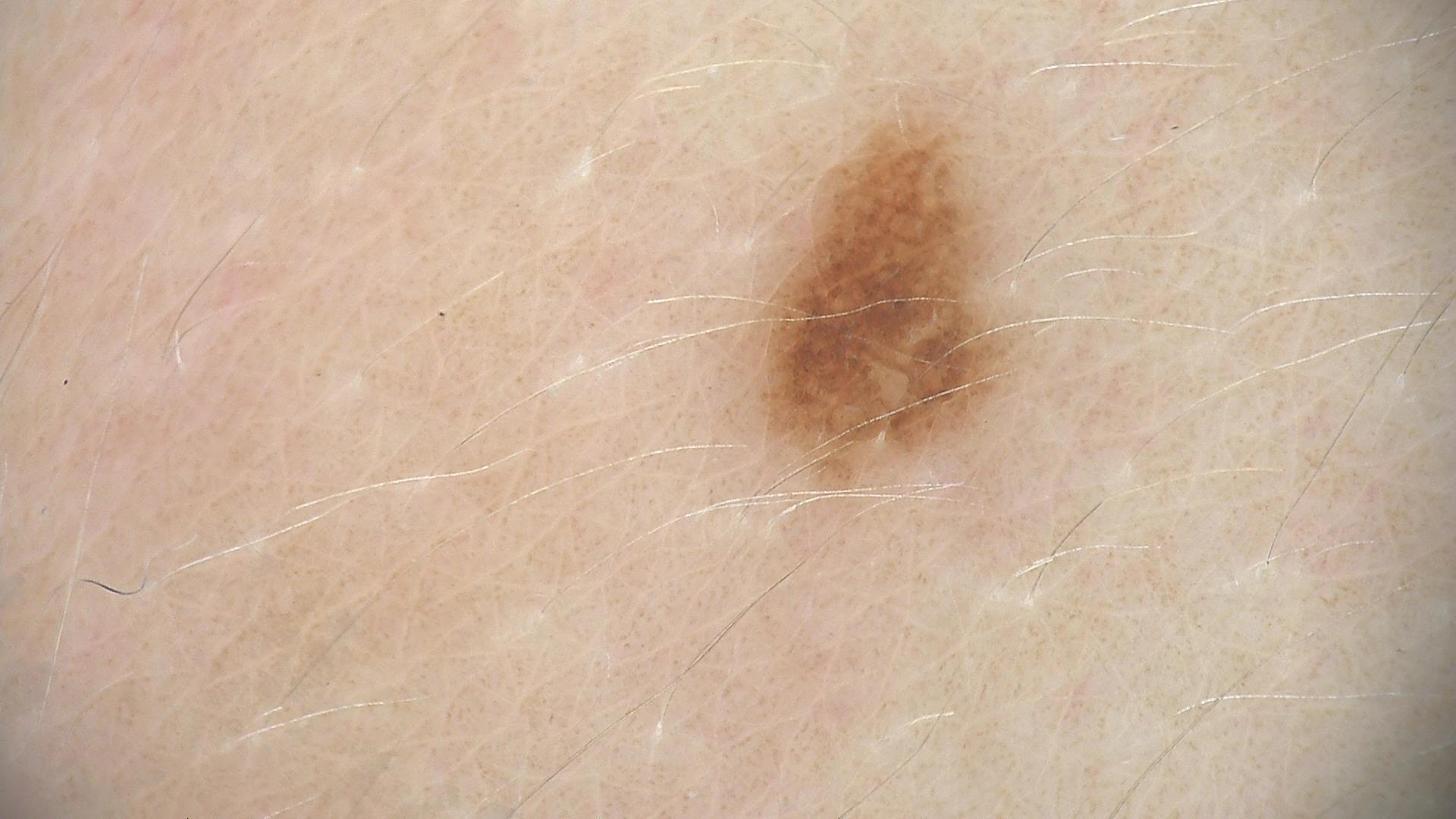Q: What is the diagnosis?
A: compound nevus (expert consensus)